This is a dermoscopic photograph of a skin lesion:
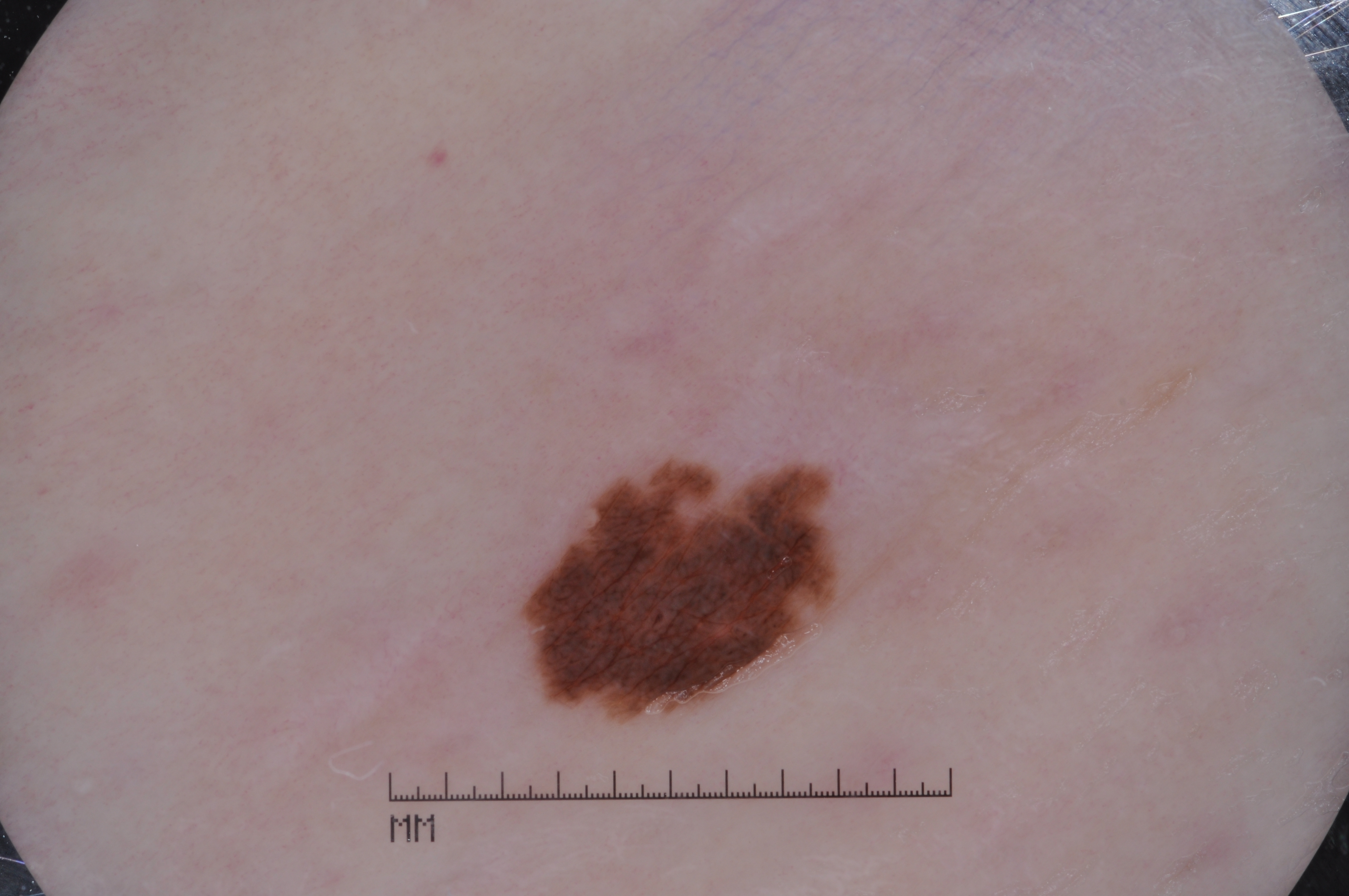| feature | finding |
|---|---|
| lesion location | 527 469 843 714 |
| extent | ~5% of the field |
| dermoscopic features not present | pigment network, milia-like cysts, streaks, and negative network |
| assessment | a melanocytic nevus, a benign lesion |